A skin lesion imaged with a dermatoscope.
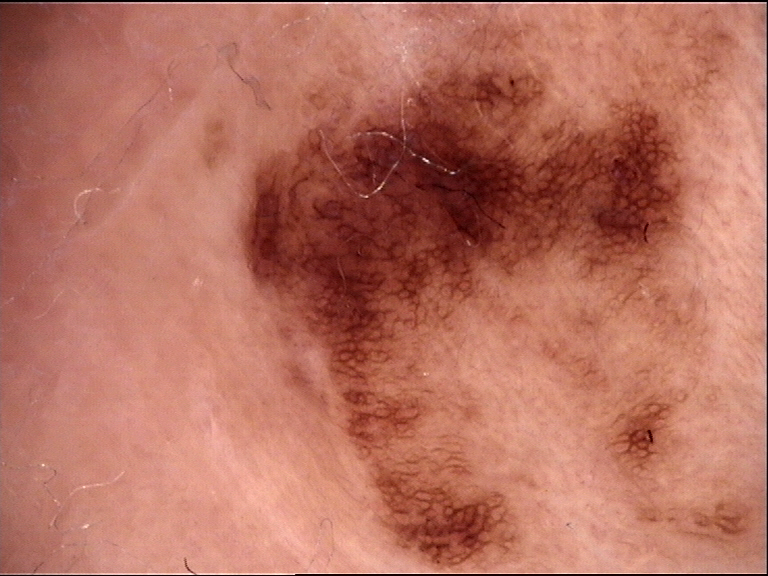Q: What was the diagnostic impression?
A: dysplastic junctional nevus (expert consensus)